Close-up view.
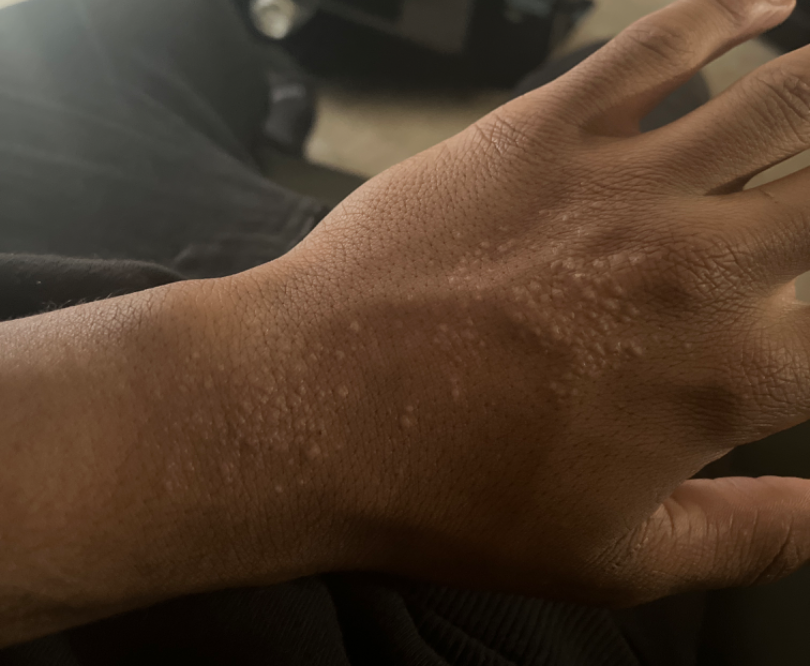Q: Could the case be diagnosed?
A: indeterminate from the photograph